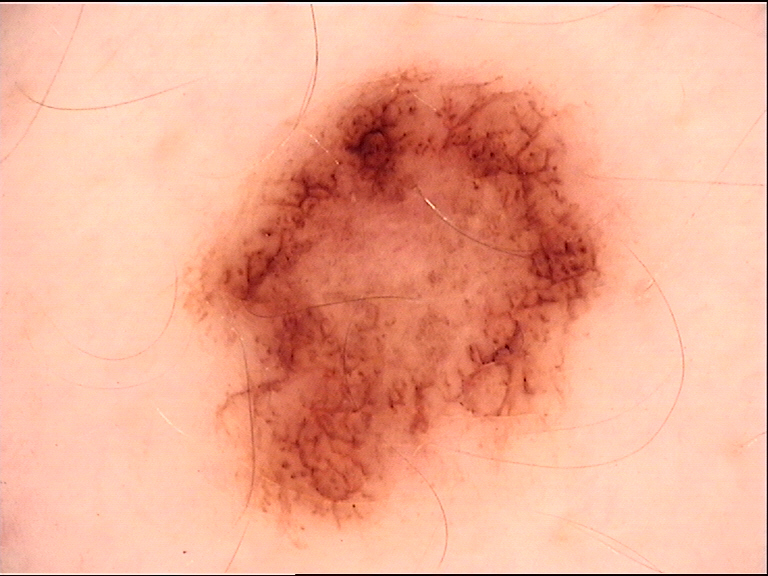Summary:
A dermatoscopic image of a skin lesion.
Impression:
The diagnostic label was a dysplastic junctional nevus.